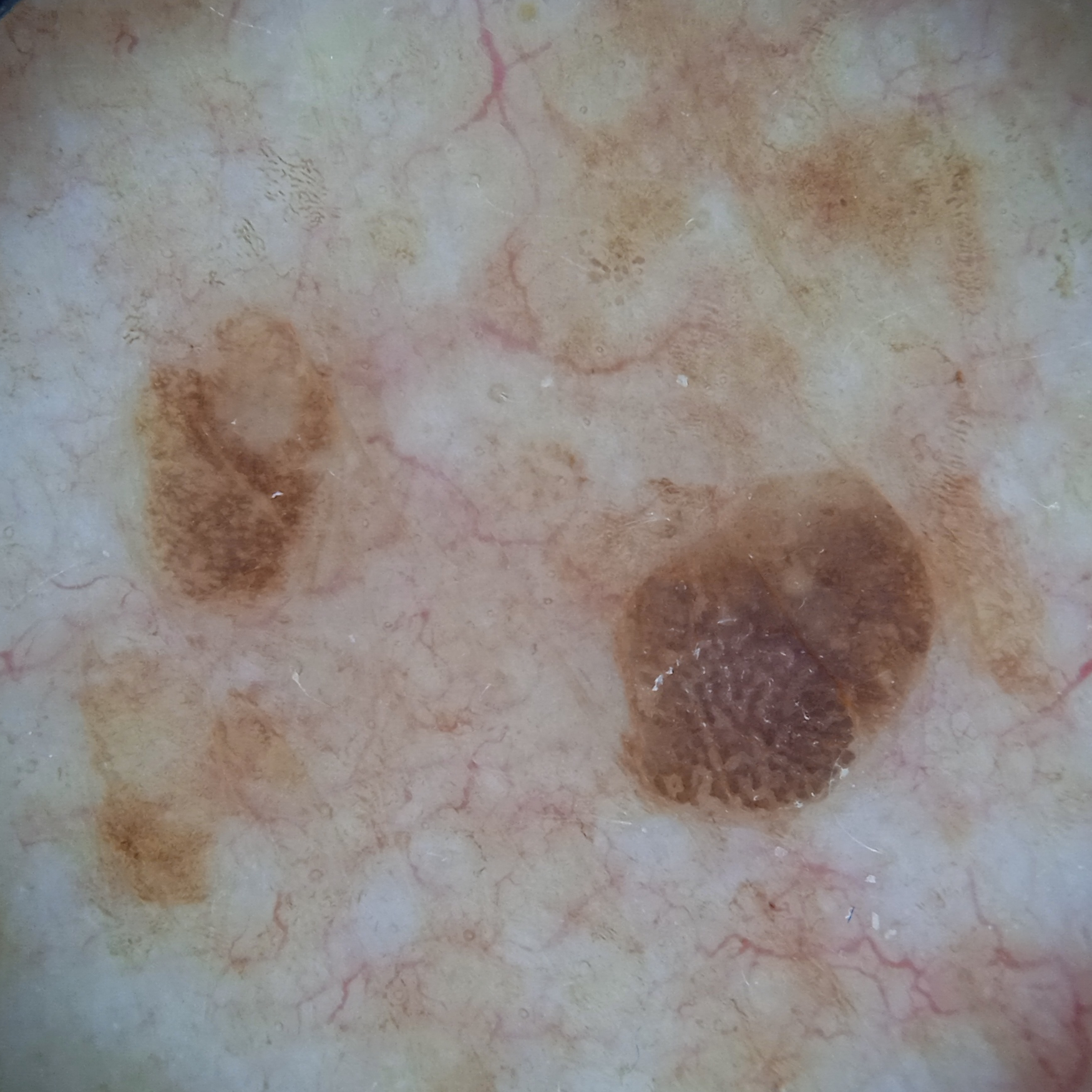A female patient age 84. A dermatoscopic image of a skin lesion. Collected as part of a research study, without a referral diagnosis. The lesion involves the torso. Measuring roughly 4.6 mm. The four-dermatologist consensus diagnosis was a seborrheic keratosis; all four reviewers agreed.